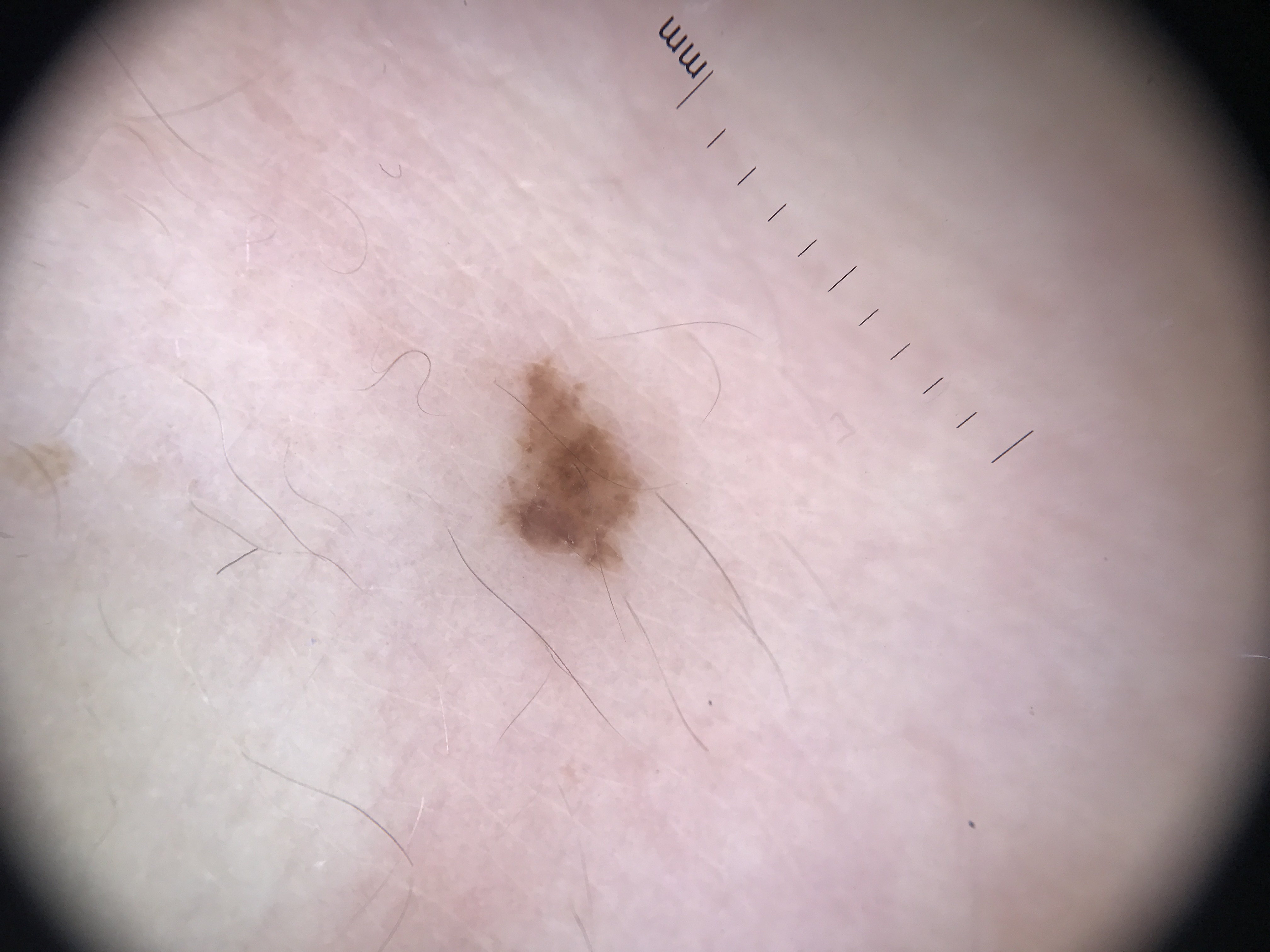Q: What is the imaging modality?
A: dermoscopy
Q: What is this lesion?
A: dysplastic junctional nevus (expert consensus)